The patient reports no immunosuppression; imaged for a research study, with no referral diagnosis recorded; the patient says their skin tans without first burning; a female patient 78 years of age; the patient describes having numerous moles:
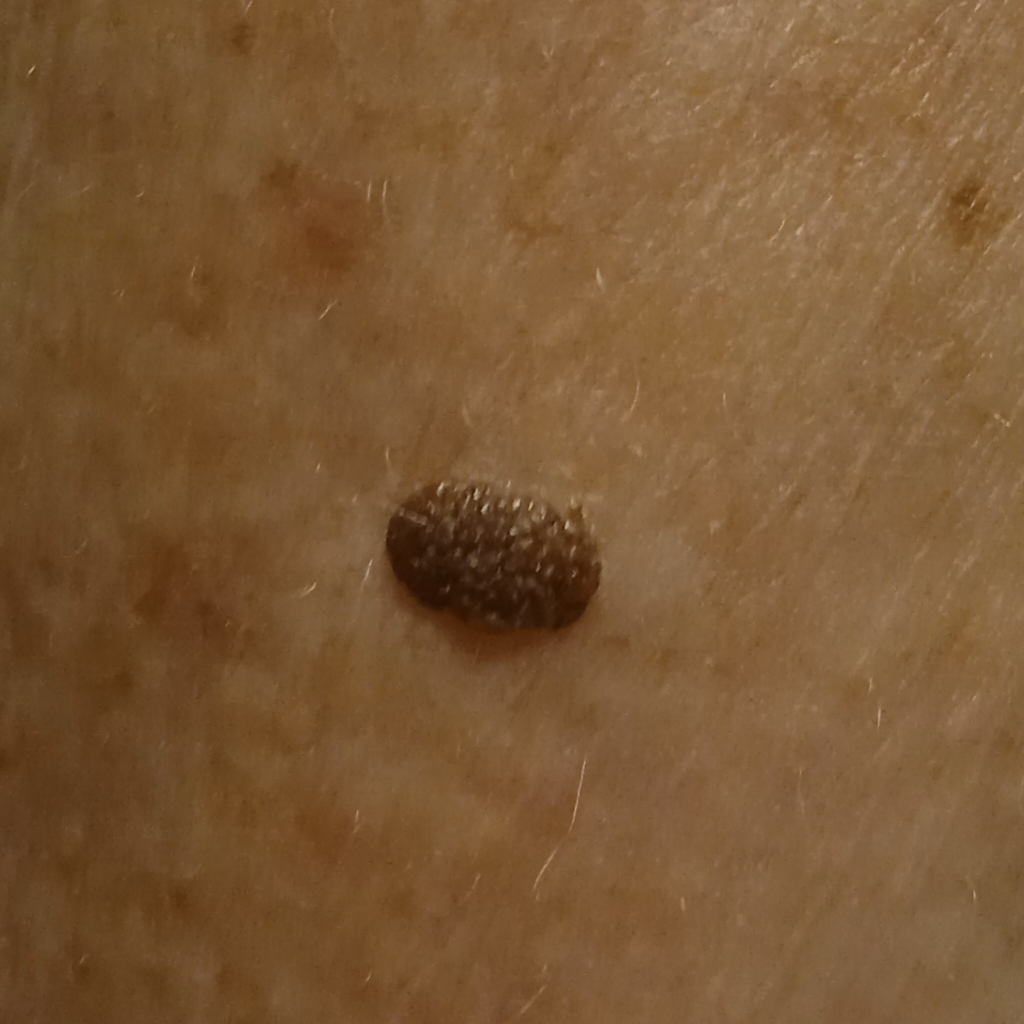The lesion is located on an arm. The dermatologists' assessment was a seborrheic keratosis.